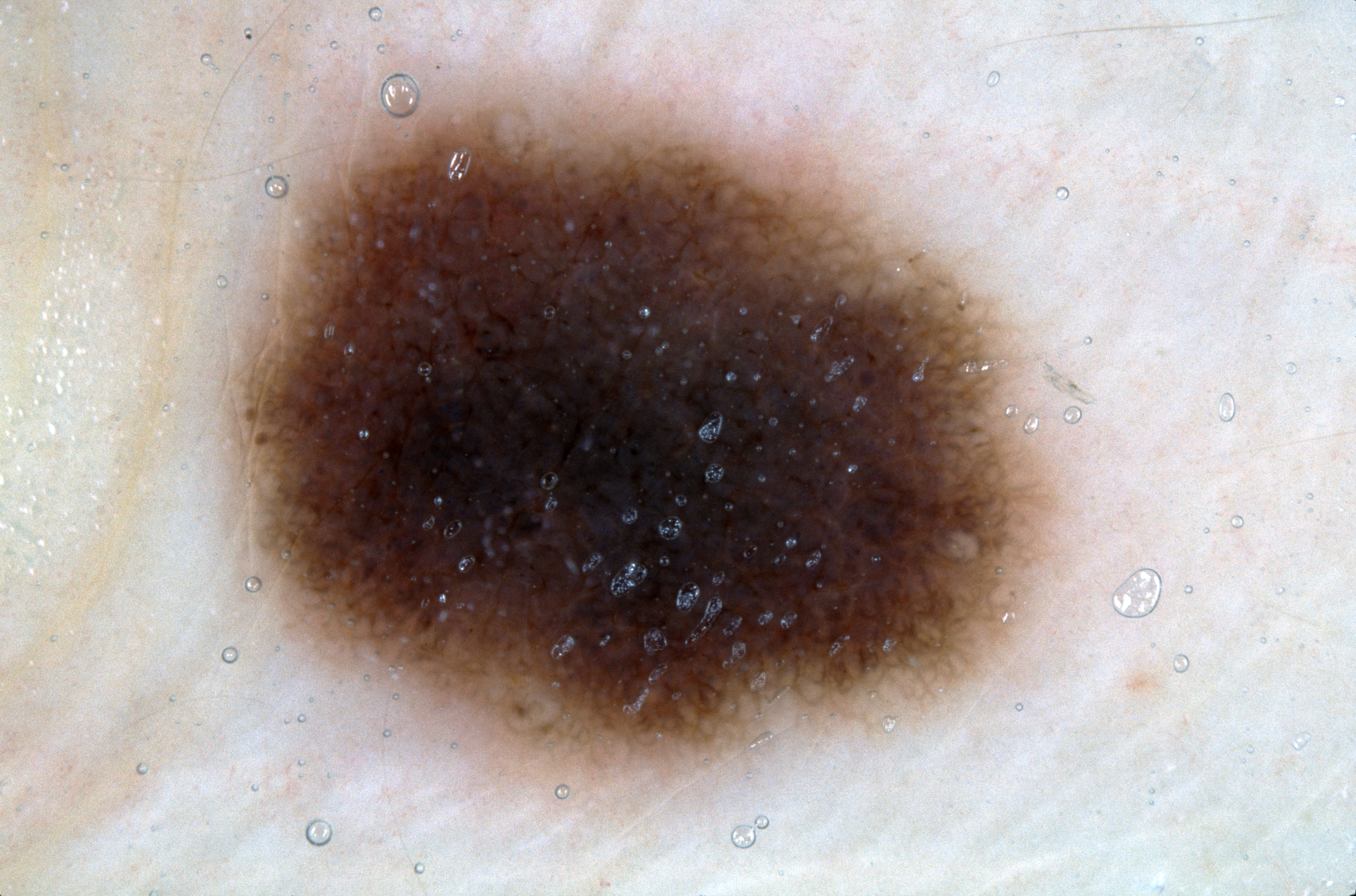modality = dermoscopy
dermoscopic pattern = pigment network
lesion location = left=232, top=105, right=1039, bottom=768
diagnostic label = a melanocytic nevus